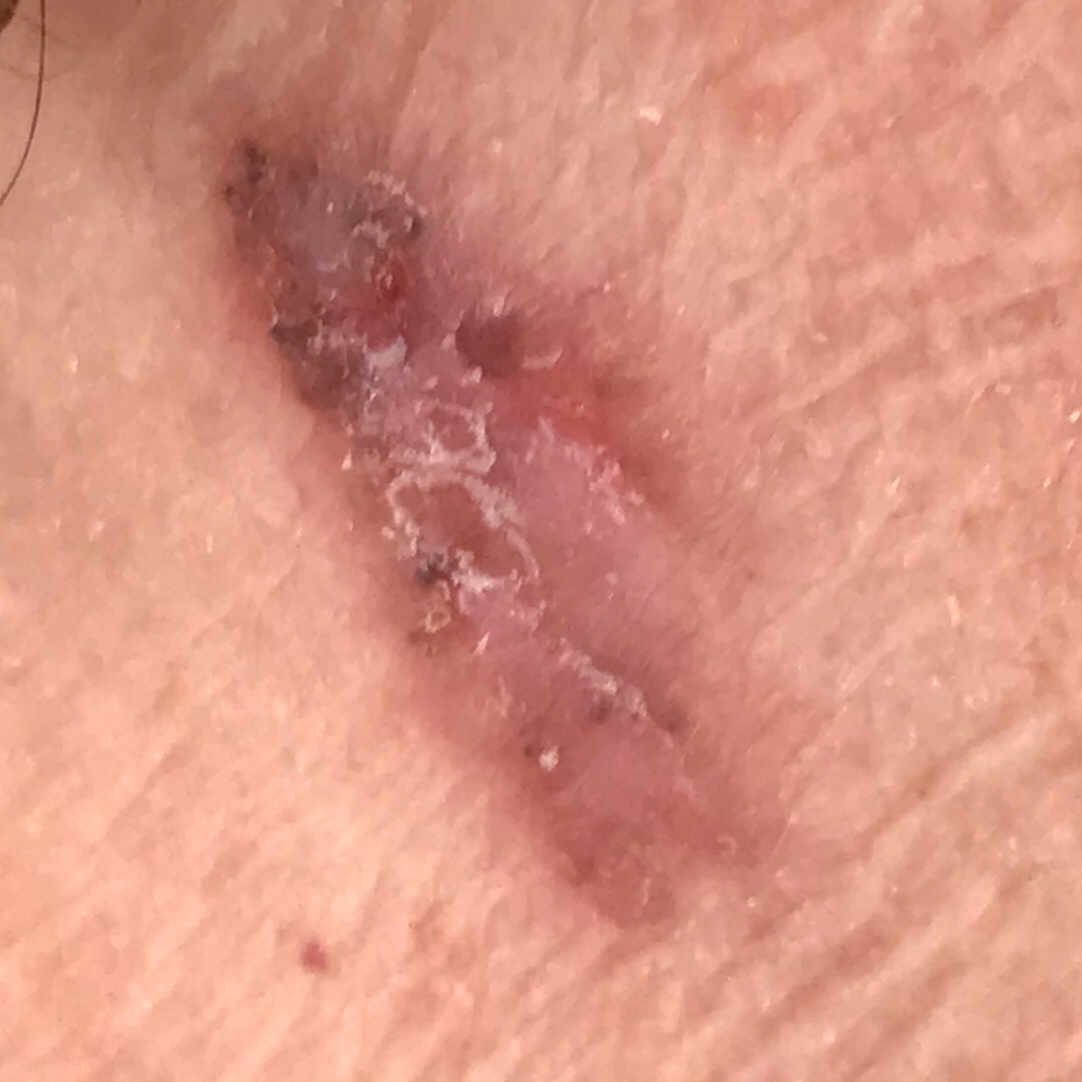Conclusion:
The biopsy diagnosis was a basal cell carcinoma.